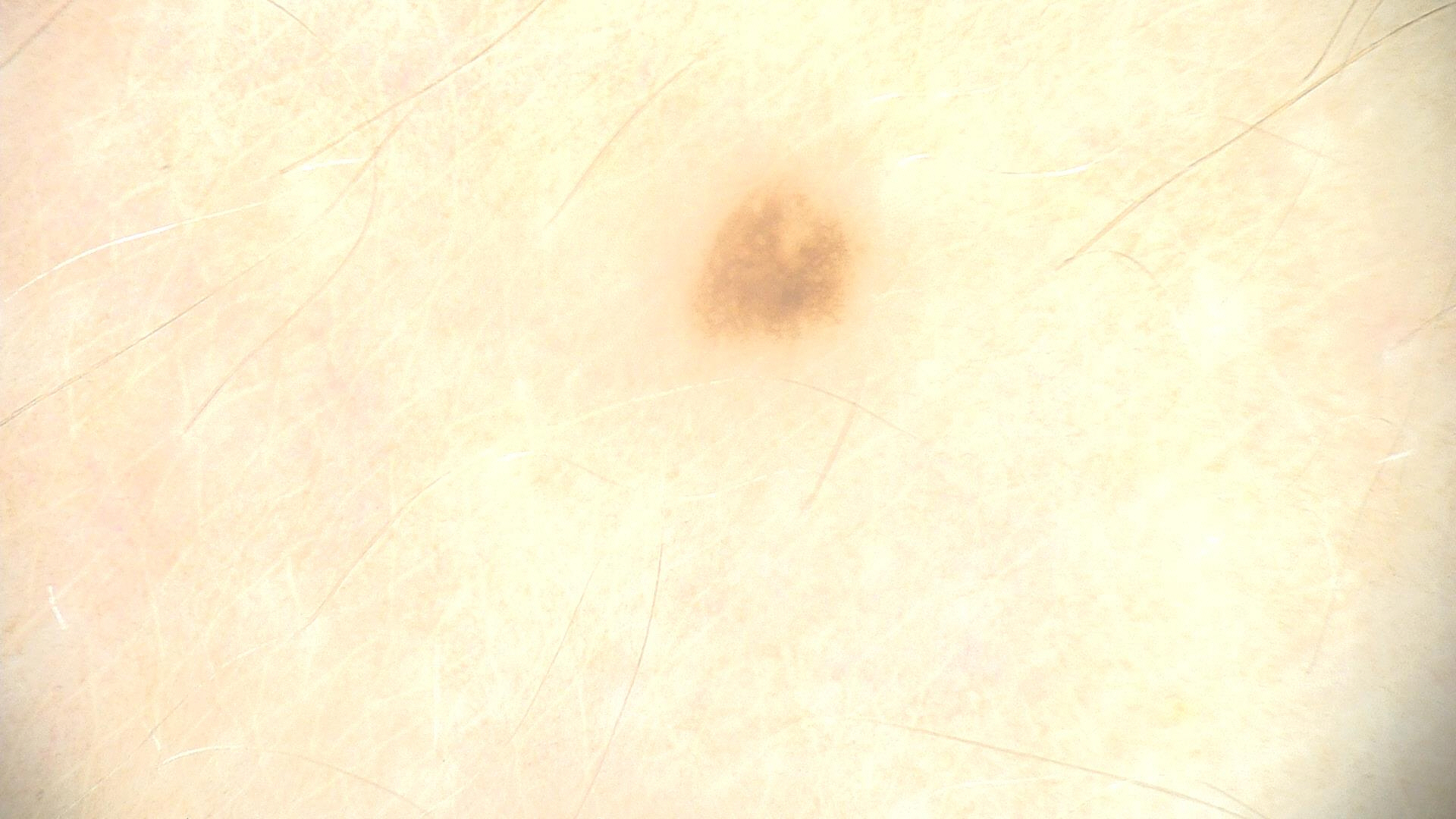The diagnostic label was a dysplastic junctional nevus.